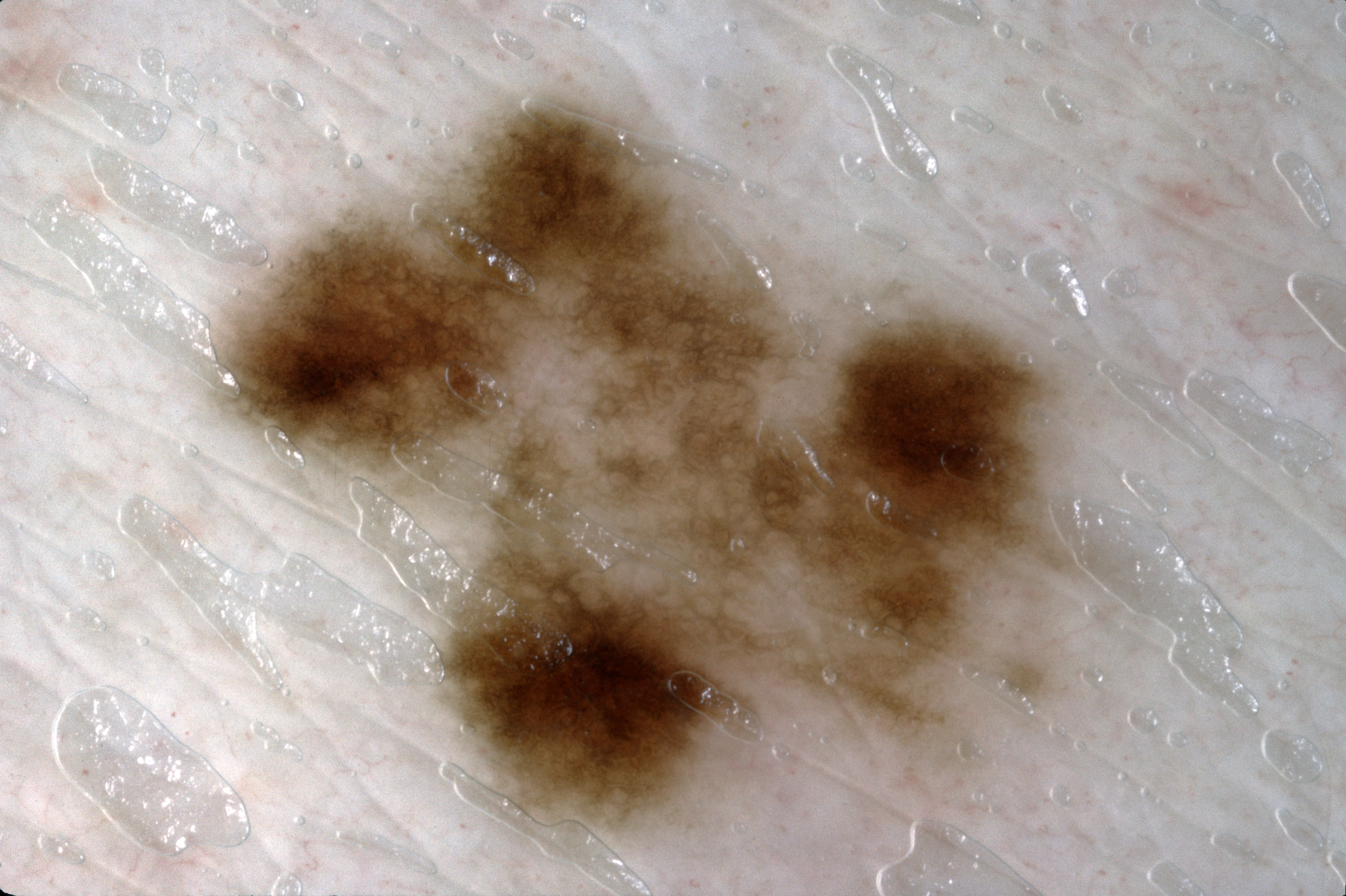A dermoscopic image of a skin lesion.
As (left, top, right, bottom), the lesion occupies the region box(217, 95, 1121, 837).
Dermoscopic examination shows pigment network; no milia-like cysts, negative network, or streaks.
Histopathologically confirmed as a melanoma.